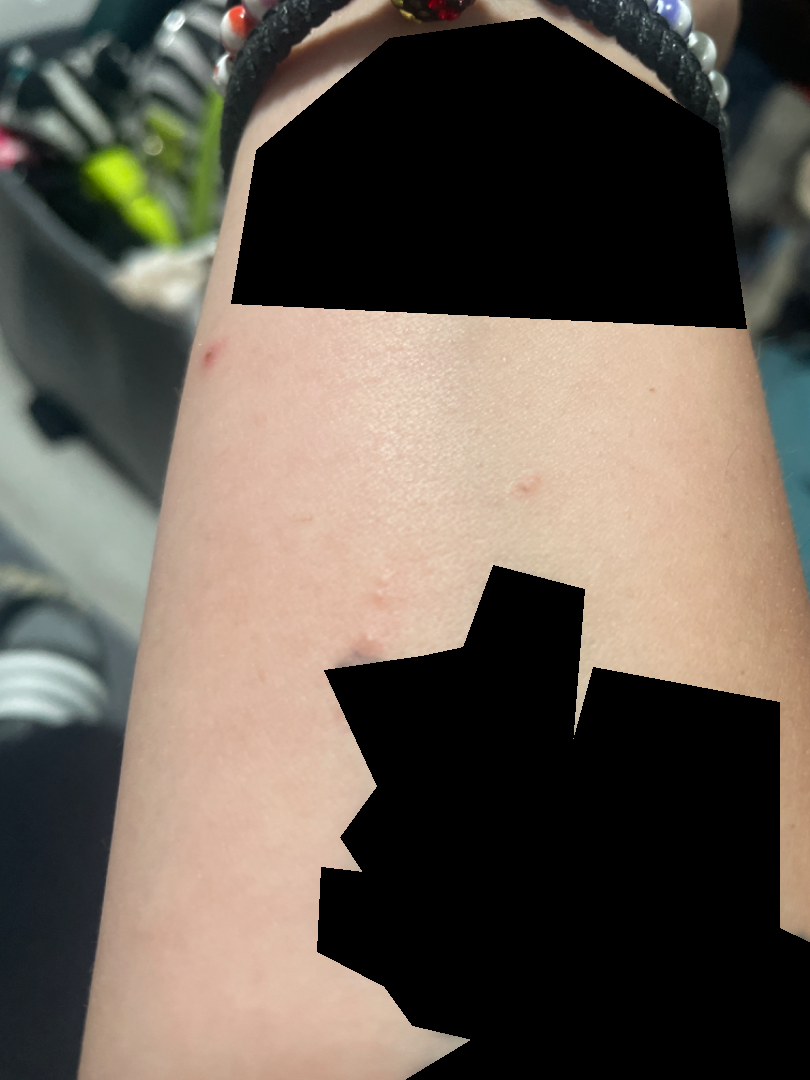The reviewing dermatologist was unable to assign a differential diagnosis from the image. The photograph was taken at an angle. The affected area is the arm.